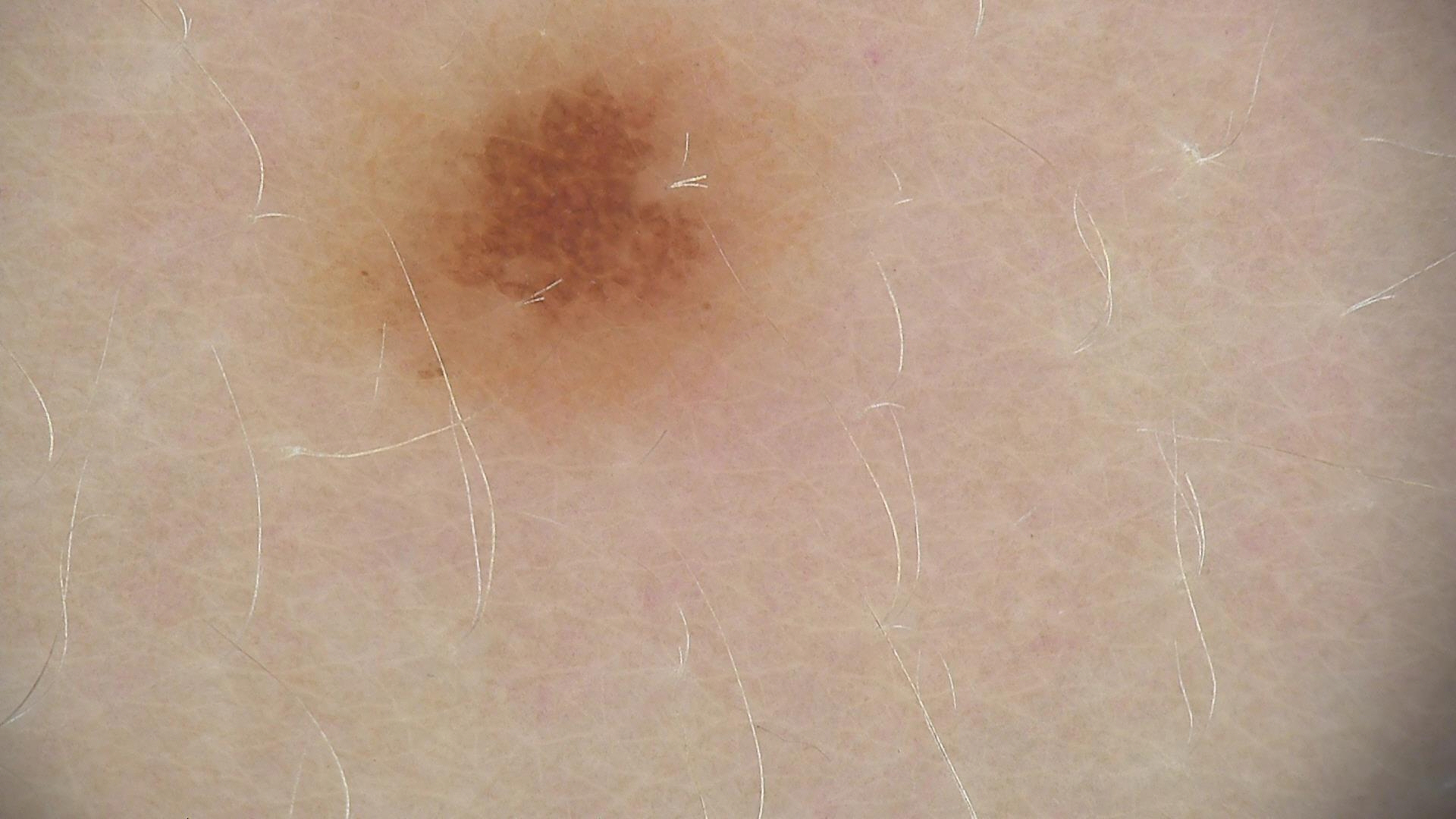Impression:
Classified as a dysplastic junctional nevus.